Dermoscopy of a skin lesion.
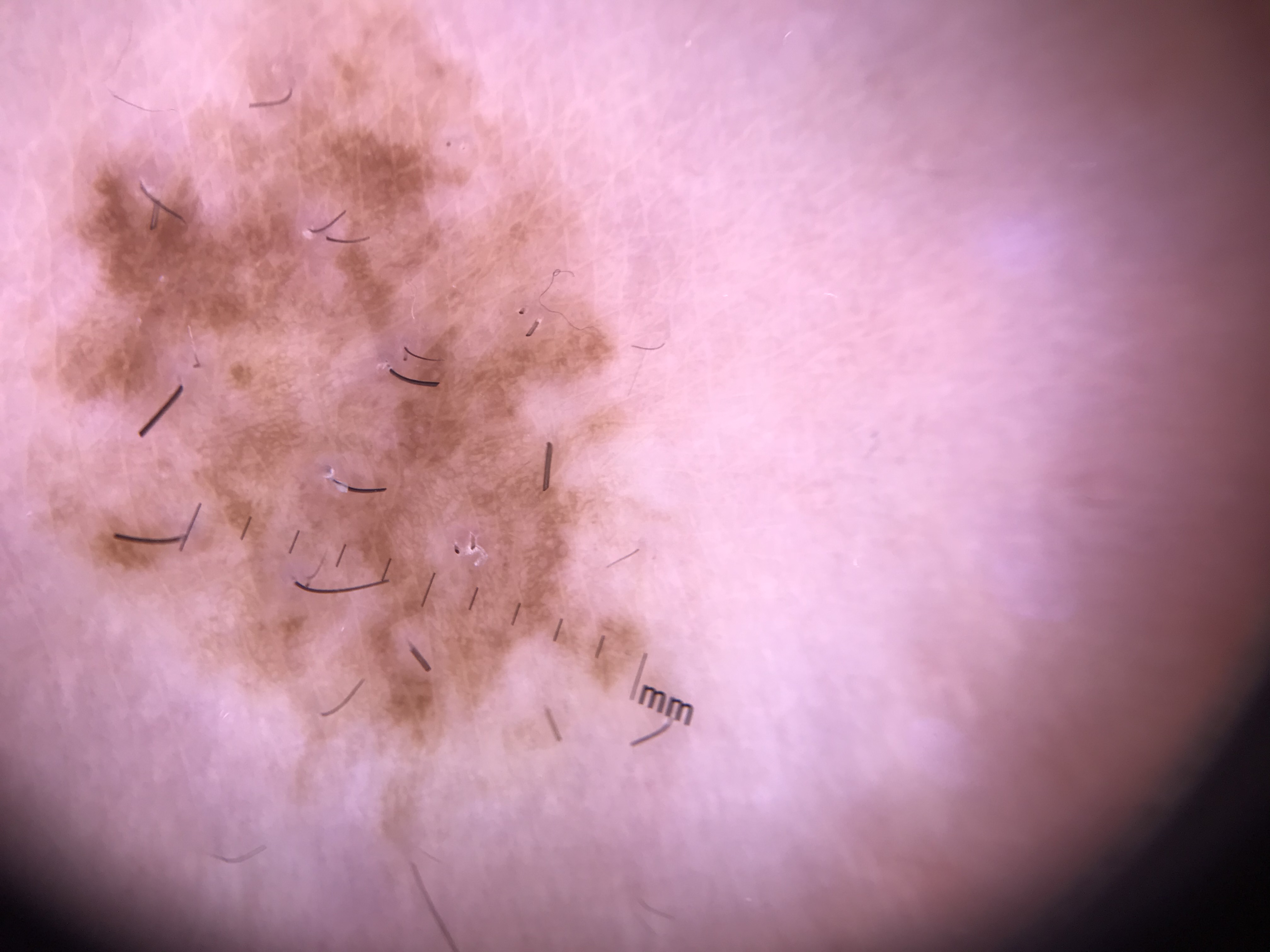Q: What kind of lesion is this?
A: banal
Q: What was the diagnostic impression?
A: congenital compound nevus (expert consensus)